Located on the leg, self-categorized by the patient as a rash, the contributor notes the lesion is raised or bumpy, this is a close-up image, symptoms reported: burning.
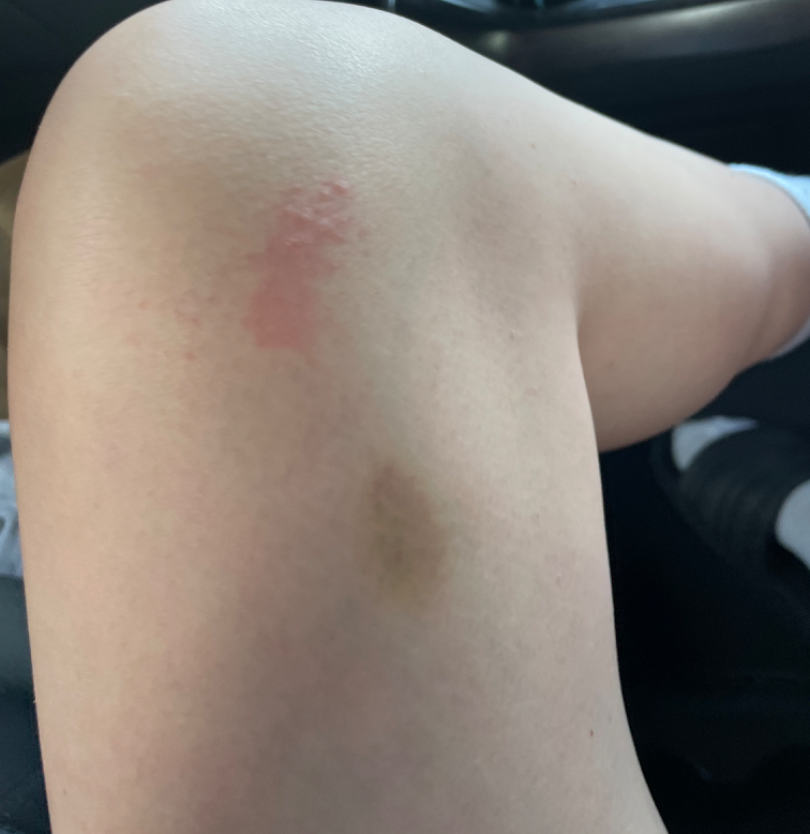One reviewing dermatologist: the impression on review was Irritant Contact Dermatitis.